A male subject 52 years of age.
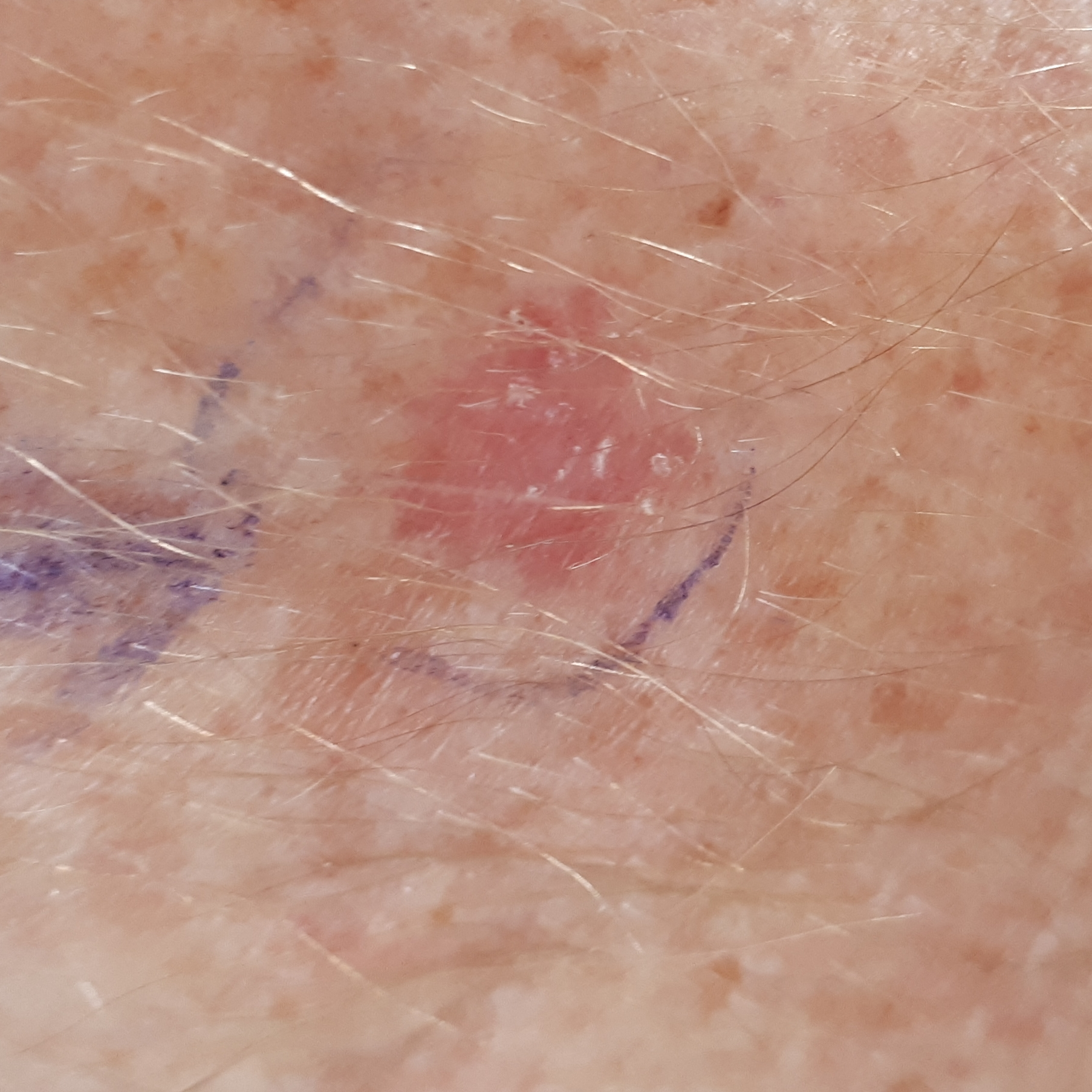reported symptoms = itching, diagnostic label = basal cell carcinoma (biopsy-proven).